The contributor is 50–59, female; this image was taken at a distance; the leg is involved — 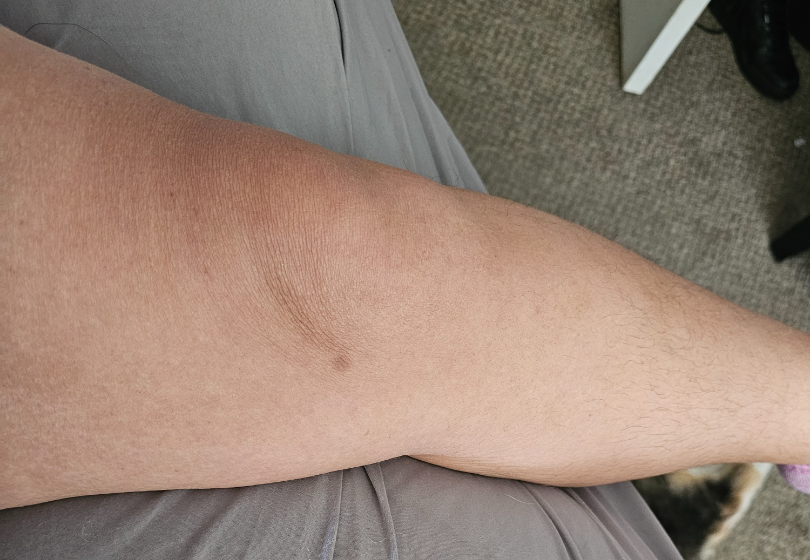On remote dermatologist review, favoring Dermatofibroma; less likely is Melanocytic Nevus; less probable is Lichen Simplex Chronicus.